A subject aged 86:
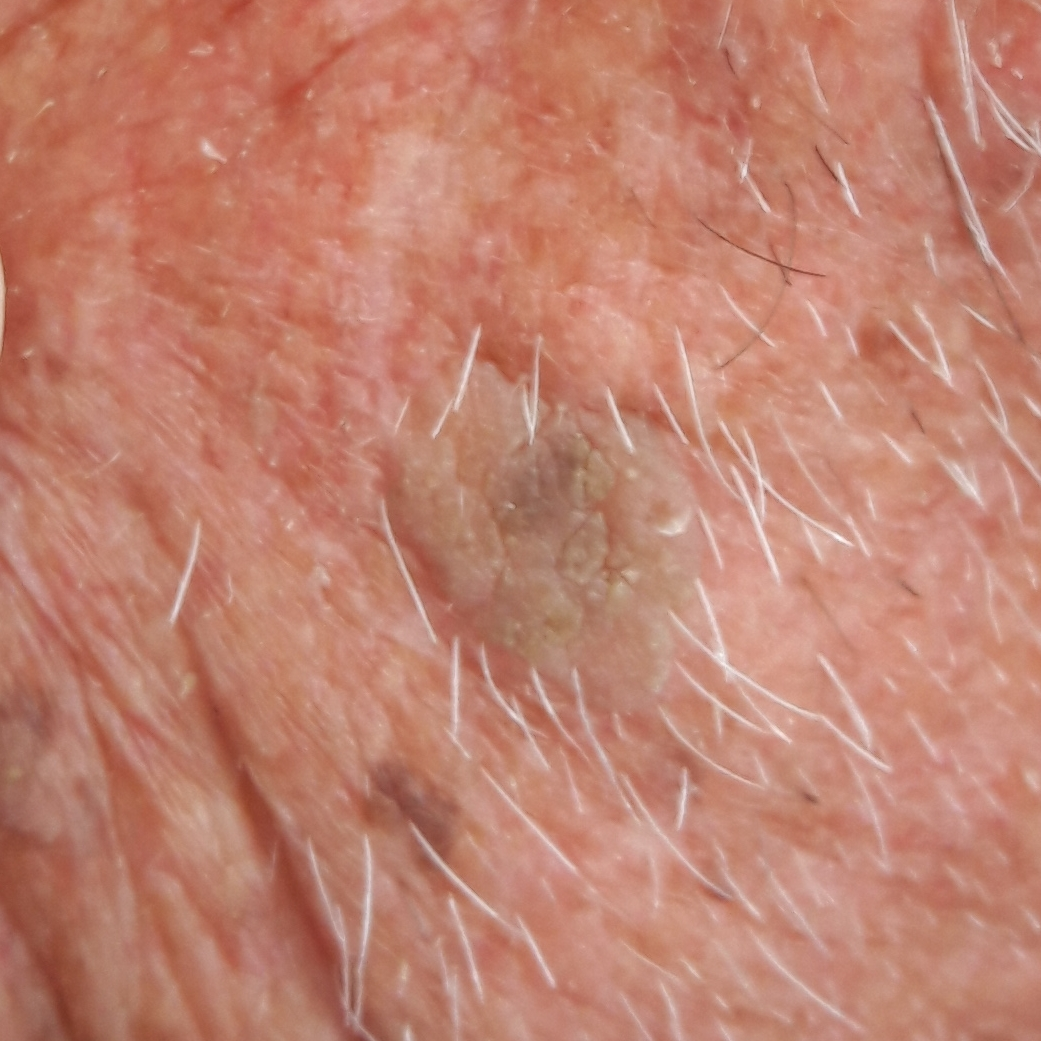symptoms = itching, elevation; diagnosis = seborrheic keratosis (clinical consensus).